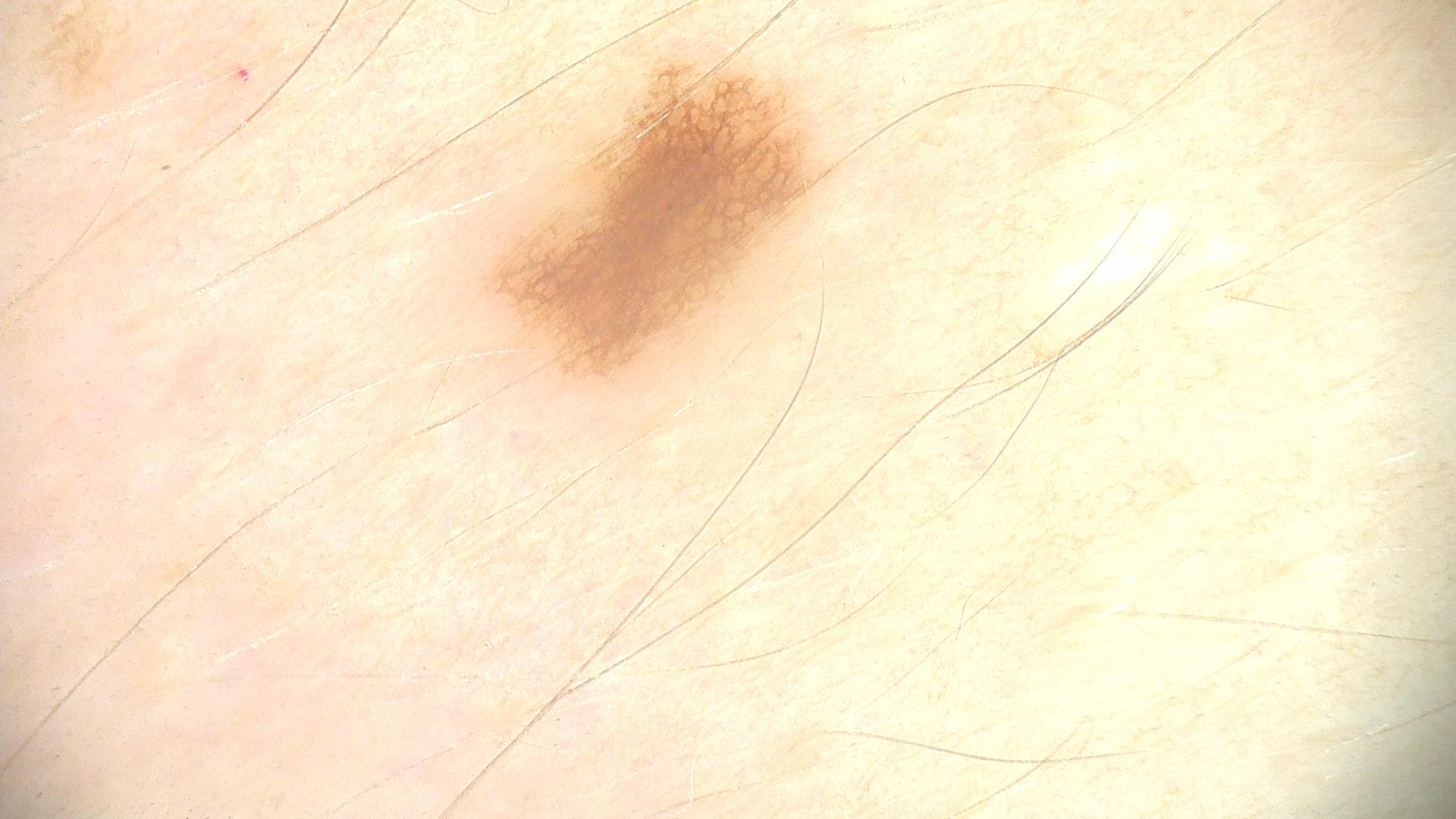Impression: Diagnosed as a dysplastic junctional nevus.